Female contributor, age 18–29 · a close-up photograph: 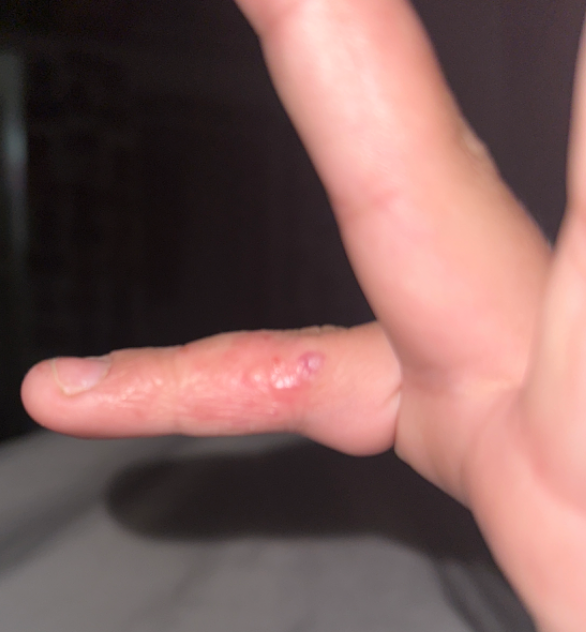The skin condition could not be confidently assessed from this image.
Reported lesion symptoms include bothersome appearance, itching and burning.
Self-categorized by the patient as a rash.
The condition has been present for three to twelve months.
No constitutional symptoms were reported.
Texture is reported as raised or bumpy, rough or flaky and fluid-filled.